A dermoscopic close-up of a skin lesion.
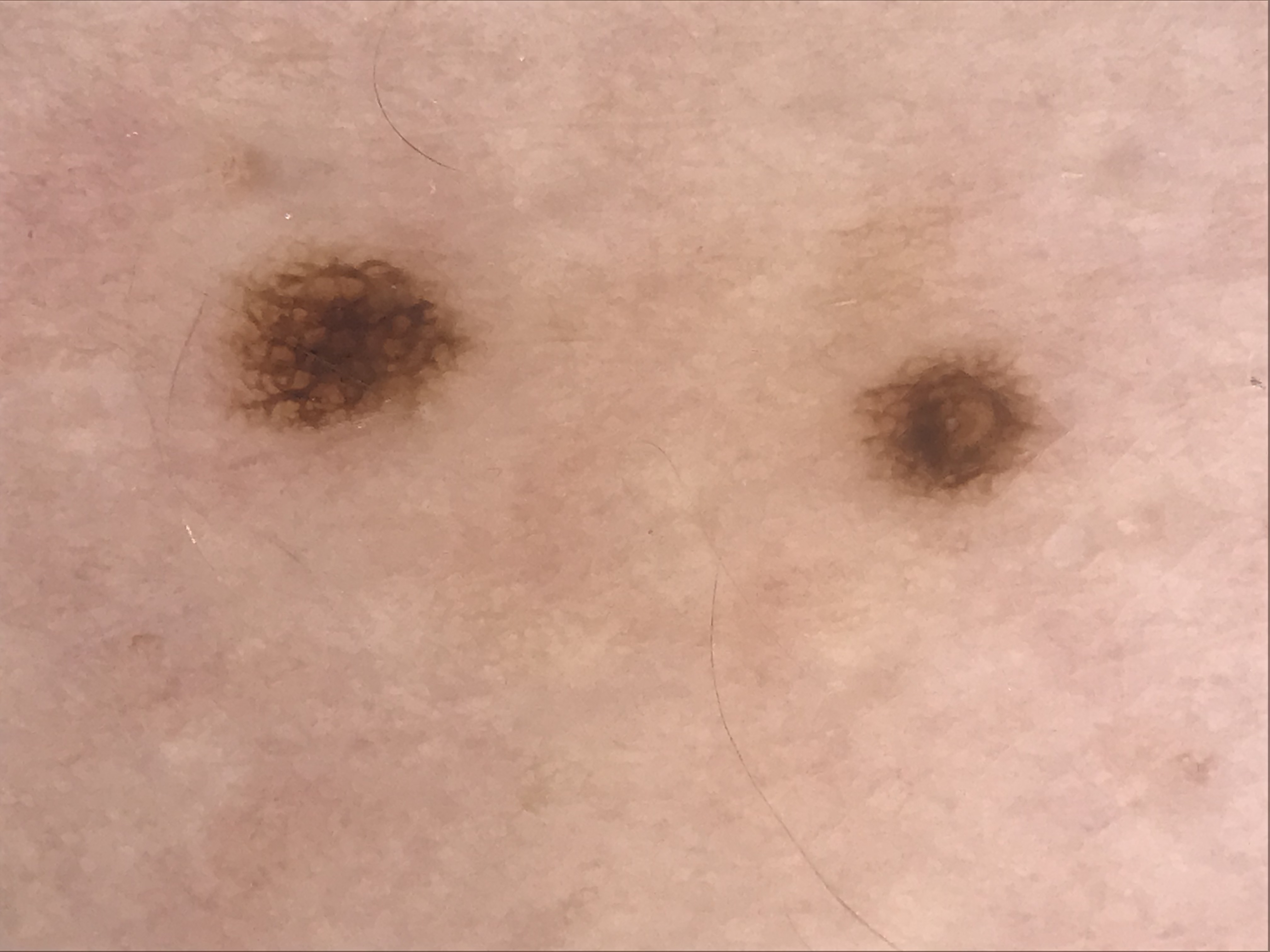label = dysplastic junctional nevus (expert consensus)